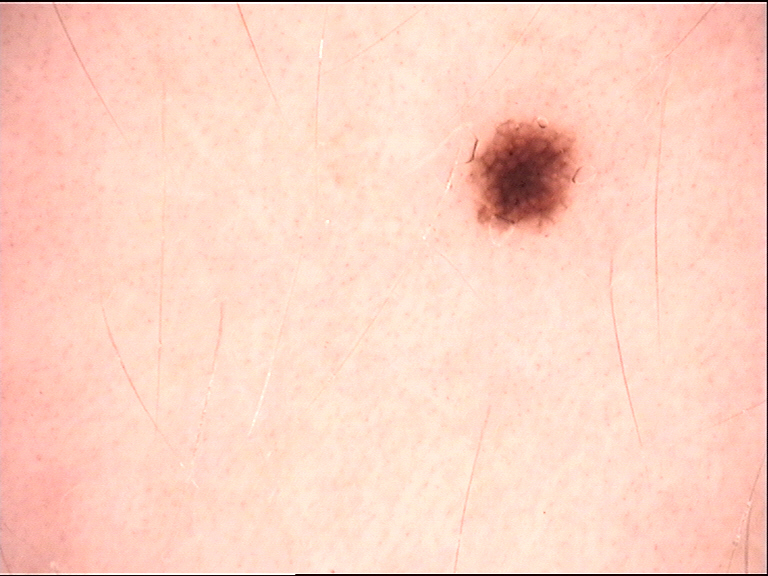Summary:
A dermatoscopic image of a skin lesion.
Conclusion:
The diagnostic label was a benign lesion — a dysplastic junctional nevus.